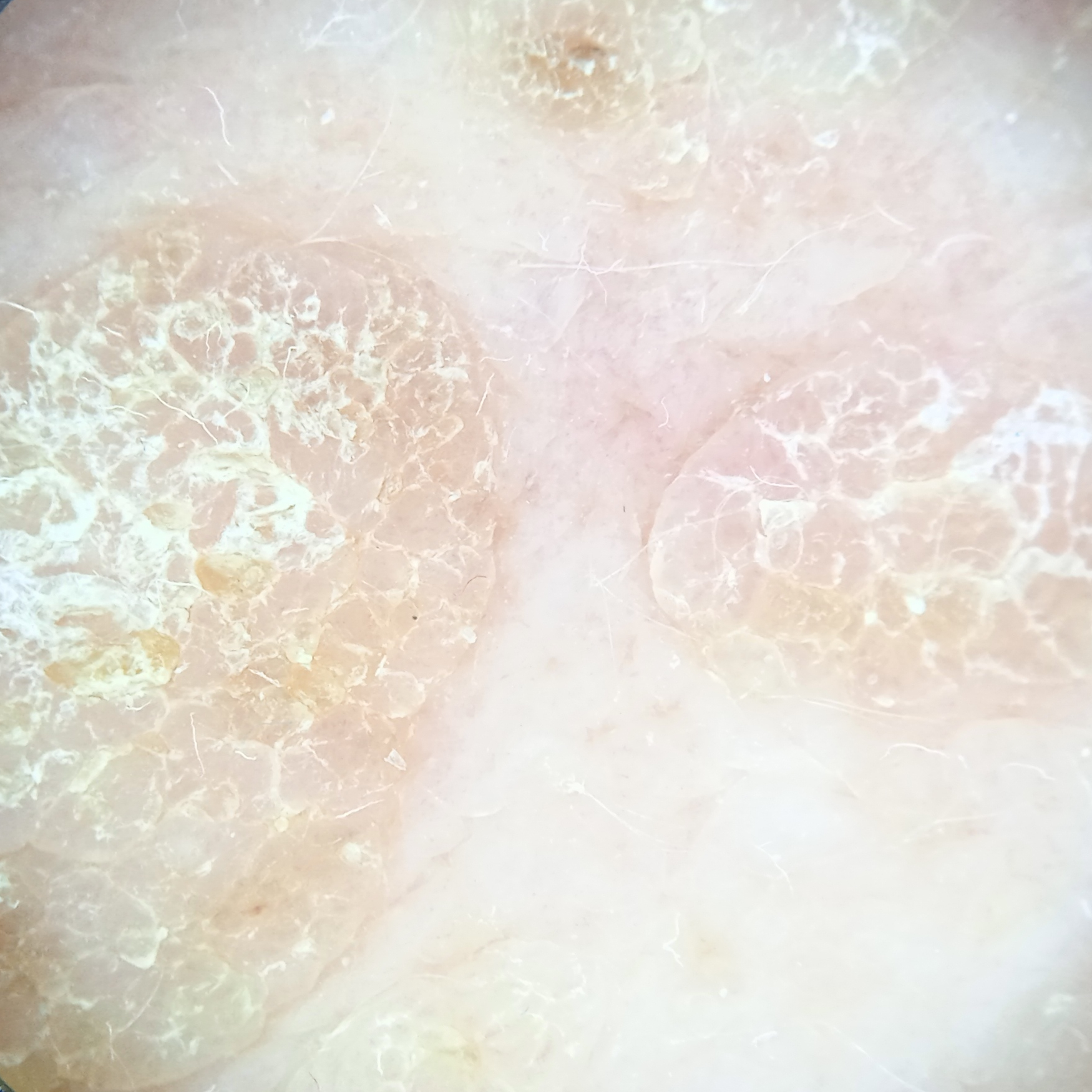A female patient aged 55.
Collected as part of a research study, without a referral diagnosis.
A dermoscopy image of a skin lesion.
The lesion is located on the back.
The dermatologists' assessment was a seborrheic keratosis.